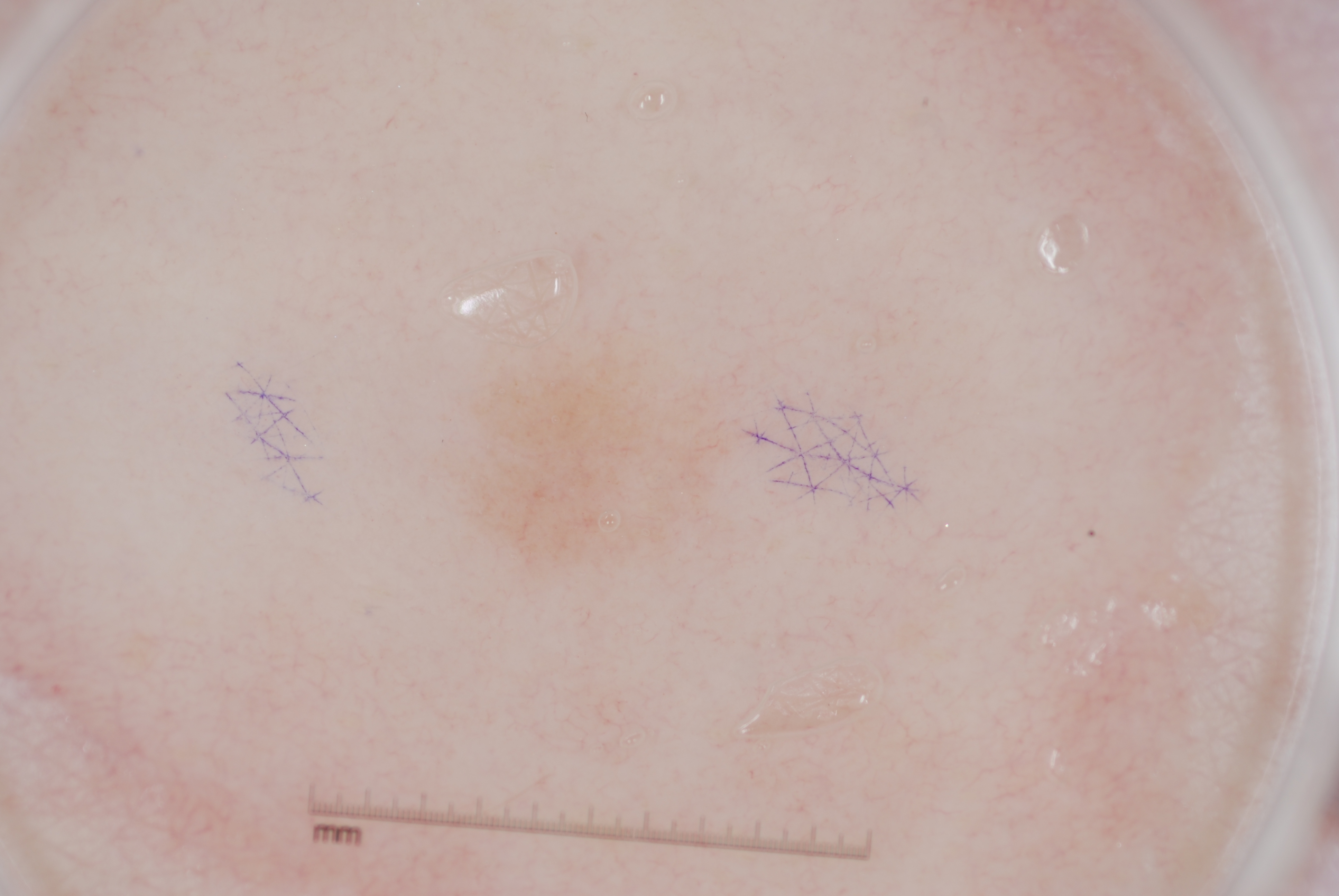A dermoscopic image of a skin lesion. The lesion takes up about 4% of the image. In (x1, y1, x2, y2) order, the lesion occupies the region 461 343 722 574. Dermoscopically, the lesion shows no negative network, milia-like cysts, streaks, or pigment network. Clinically diagnosed as a melanocytic nevus, a benign lesion.